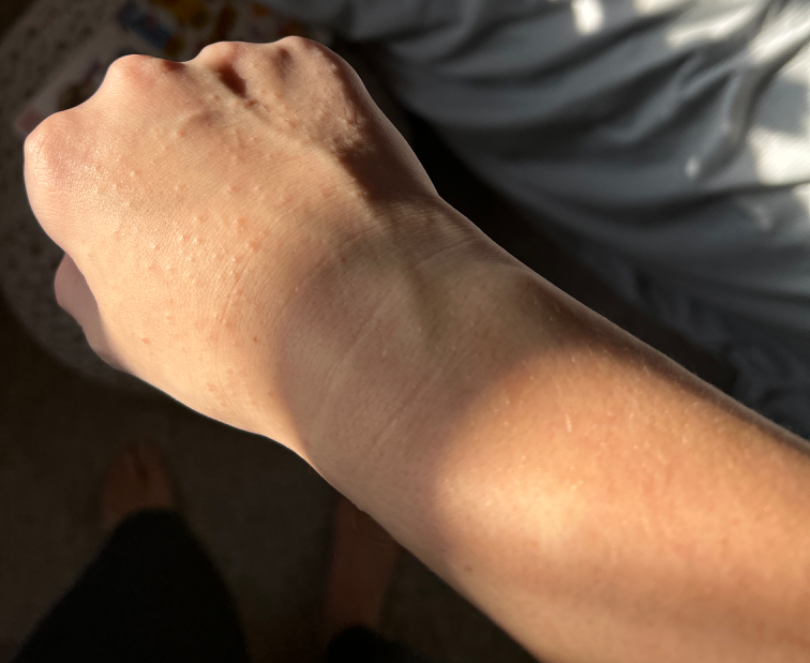History: Female patient, age 18–29. The contributor notes the condition has been present for one to four weeks. The lesion is described as raised or bumpy. The contributor notes enlargement, bothersome appearance and itching. An image taken at a distance. The back of the hand and arm are involved. Self-categorized by the patient as a rash. Impression: The leading consideration is Lichen nitidus.